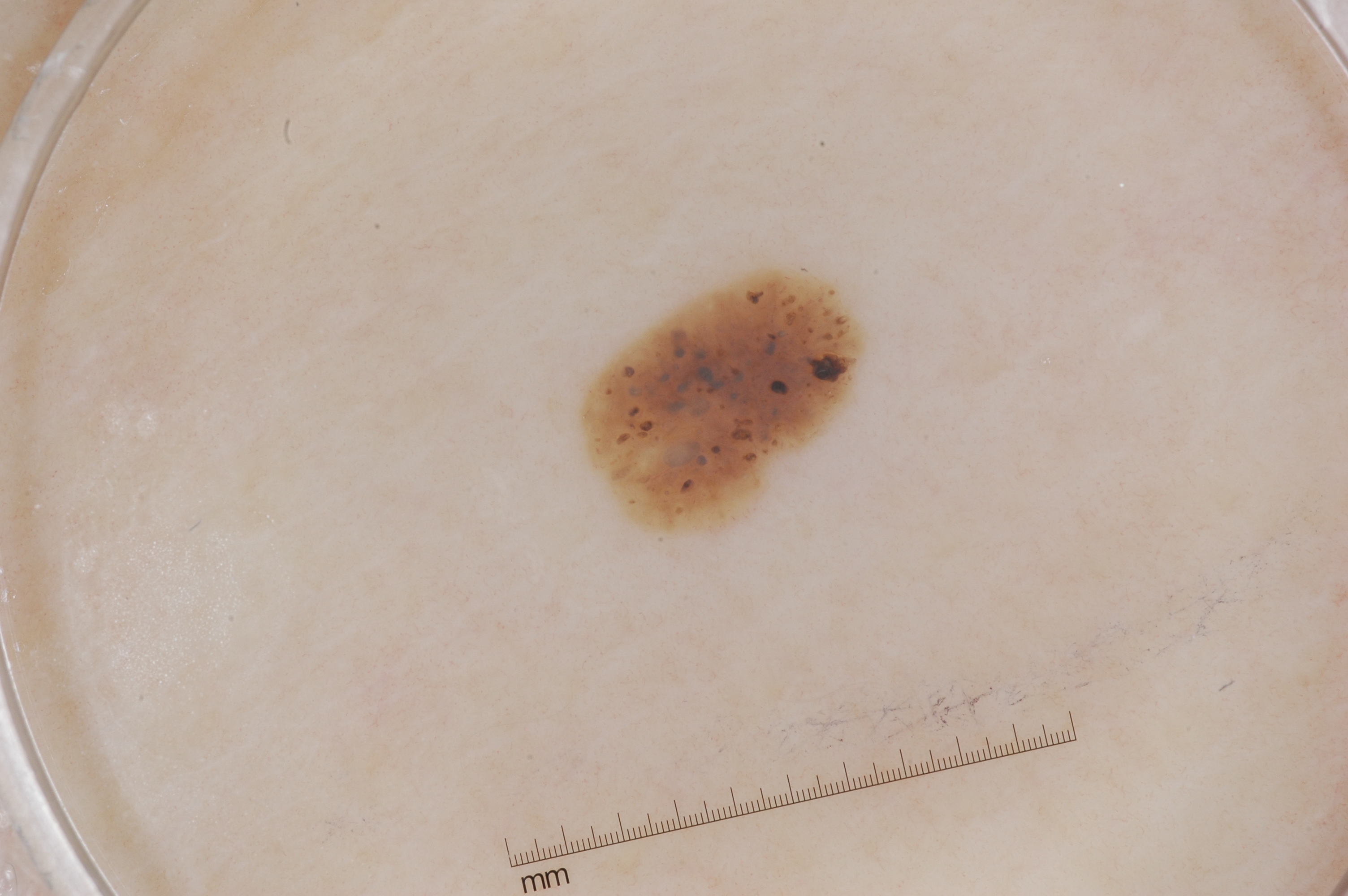Findings: A dermatoscopic image of a skin lesion. Dermoscopic examination shows milia-like cysts. The lesion covers approximately 4% of the dermoscopic field. In (x1, y1, x2, y2) order, the lesion's extent is bbox(579, 266, 853, 532). Assessment: Expert review diagnosed this as a seborrheic keratosis, a benign skin lesion.